This image was taken at an angle; the lesion involves the arm and leg — 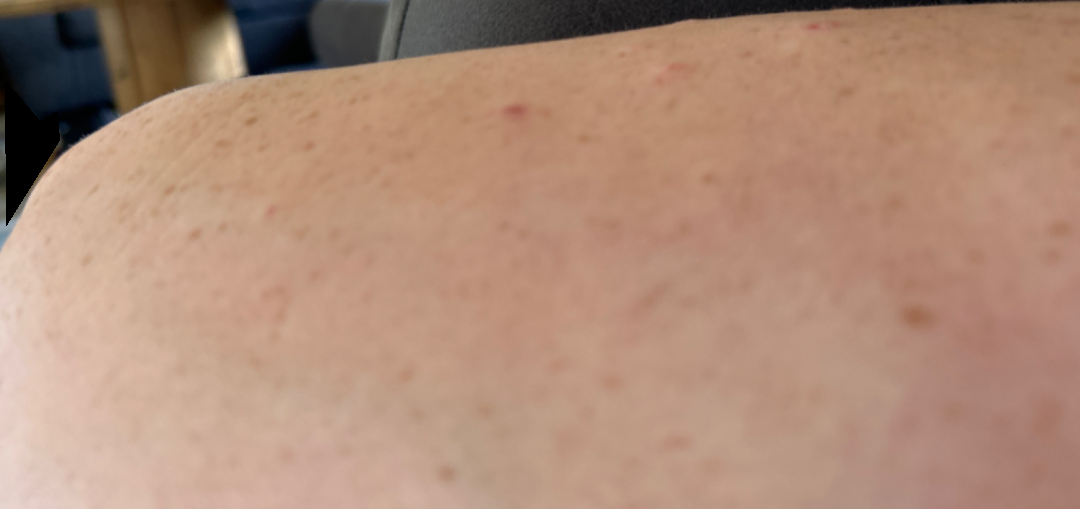other reported symptoms: none reported; differential diagnosis: the primary impression is Prurigo nodularis.